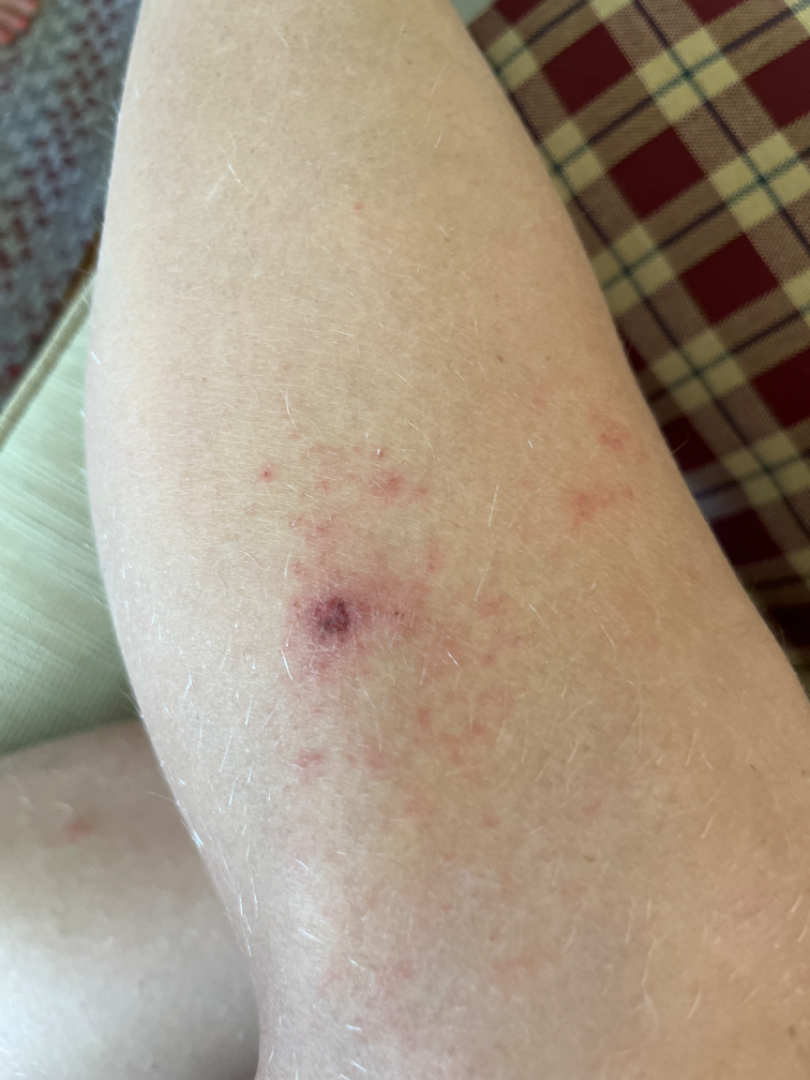assessment: not assessable